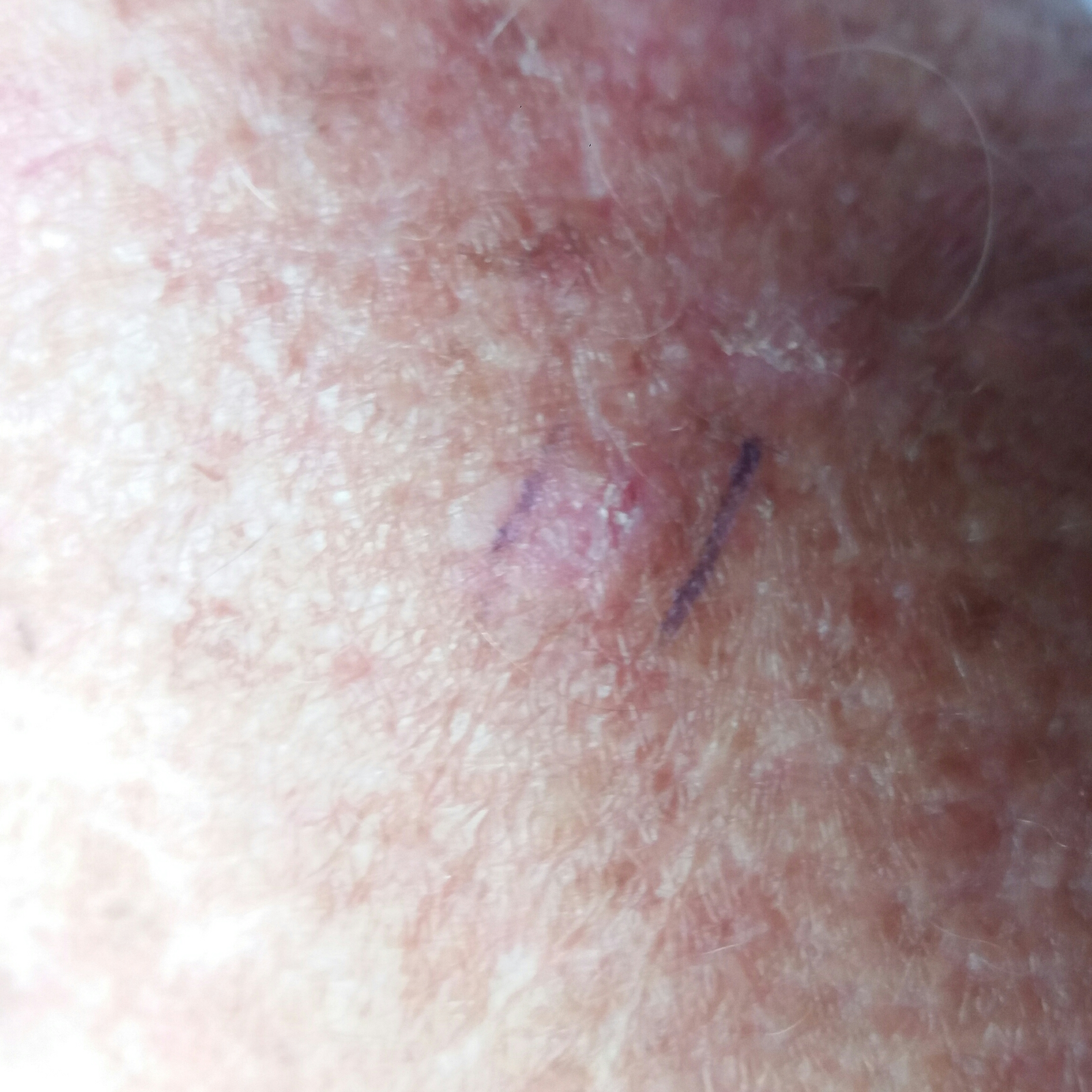A patient in their mid-60s.
A clinical close-up photograph of a skin lesion.
Located on a forearm.
The patient describes that the lesion itches, but is not elevated.
The consensus clinical diagnosis was an actinic keratosis.